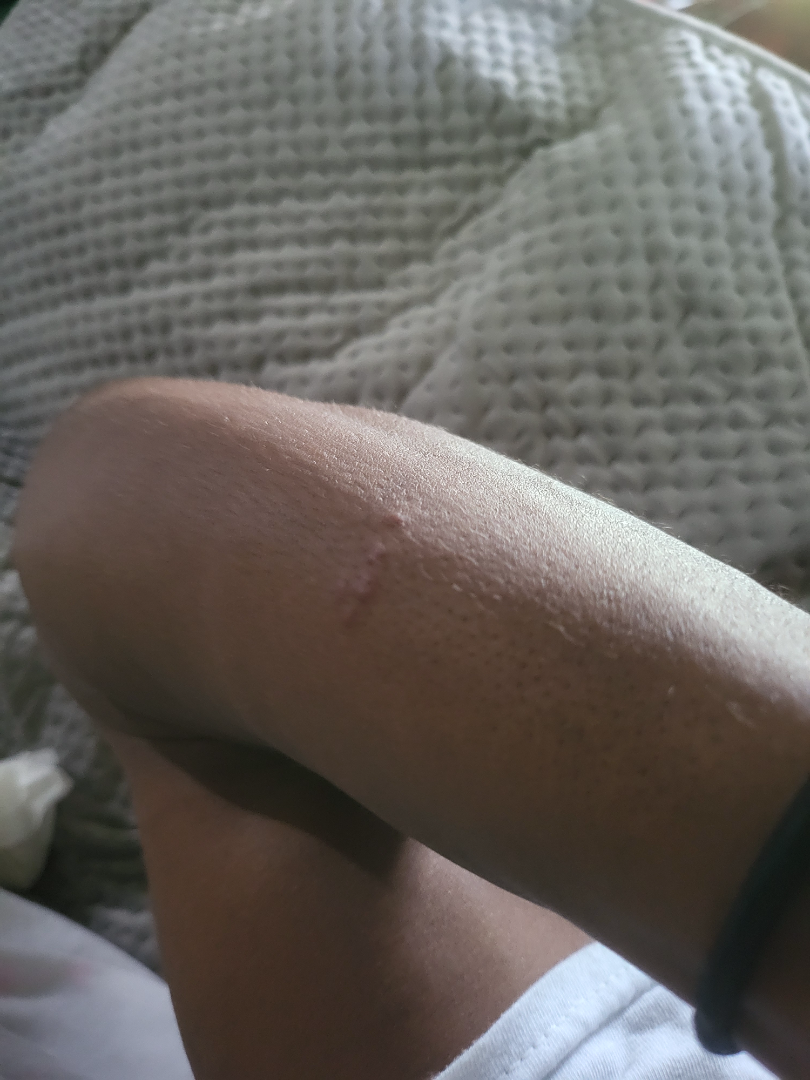| field | value |
|---|---|
| assessment | not assessable |
| shot type | close-up |
| patient | male, age 30–39 |